A close-up photograph.
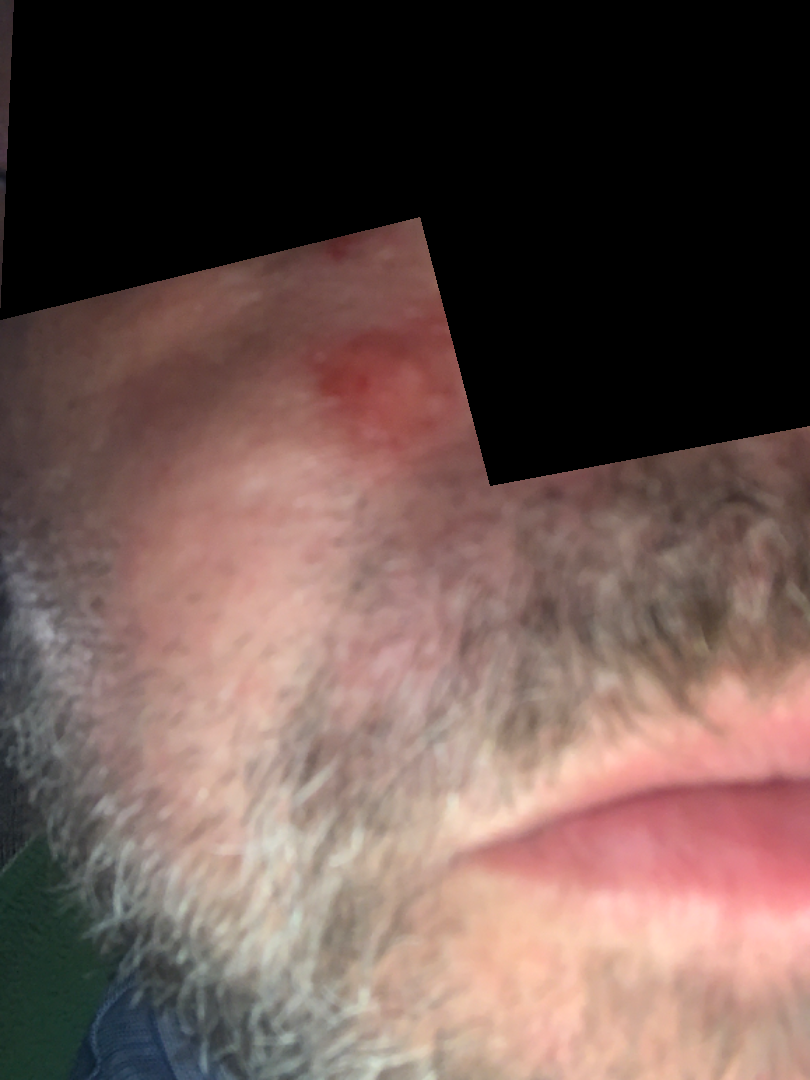Q: What was the assessment?
A: indeterminate